A dermatoscopic image of a skin lesion:
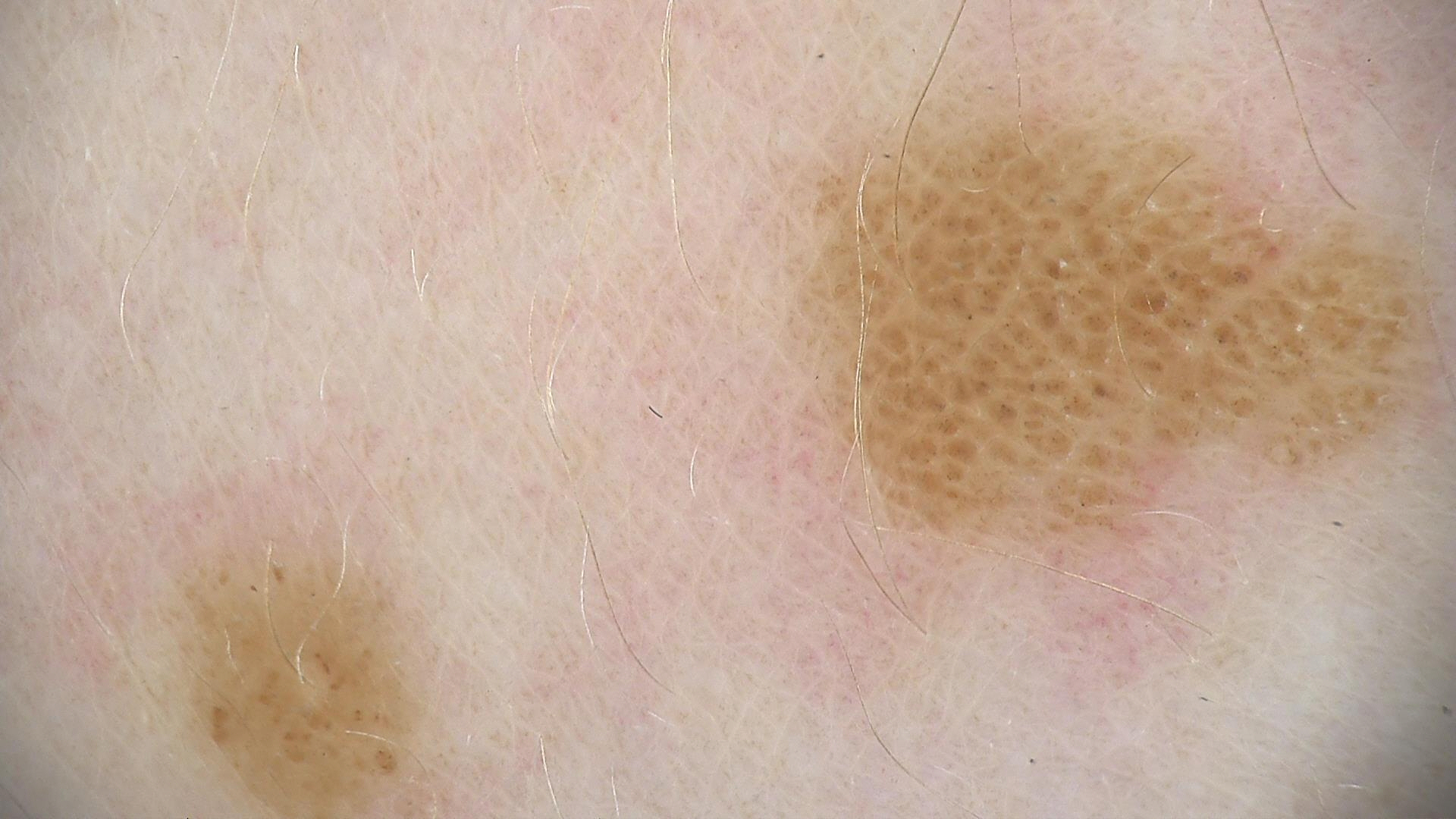Q: What is the diagnosis?
A: compound nevus (expert consensus)